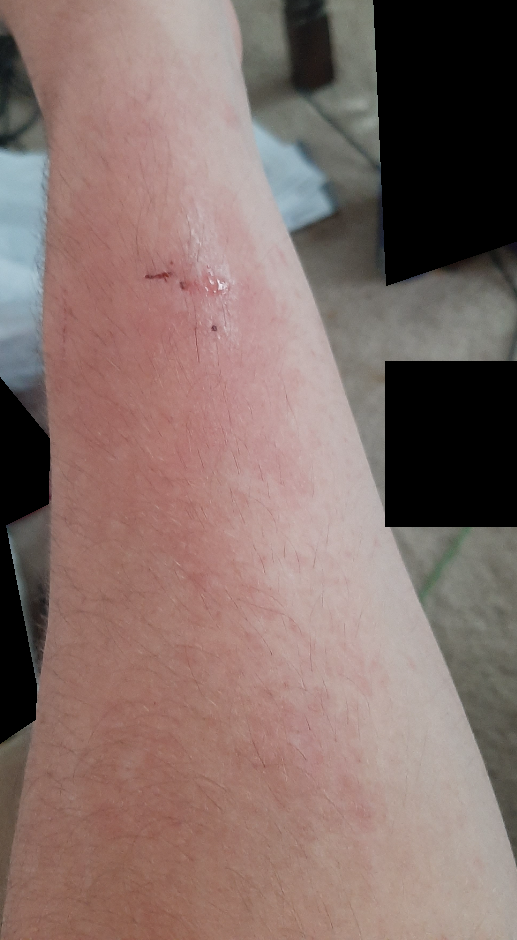Findings: The image was not sufficient for the reviewer to characterize the skin condition. Background: The patient considered this a rash. Fitzpatrick skin type II; non-clinician graders estimated Monk skin tone scale 1–2. Male subject, age 18–29. The condition has been present for less than one week. The lesion is associated with bleeding, burning and itching. The patient indicates the lesion is fluid-filled and rough or flaky. The patient also reports mouth sores. This image was taken at an angle. The lesion involves the arm and sole of the foot.